The condition has been present for about one day. Symptoms reported: pain and bothersome appearance. The affected area is the back of the torso, head or neck and front of the torso. An image taken at a distance: 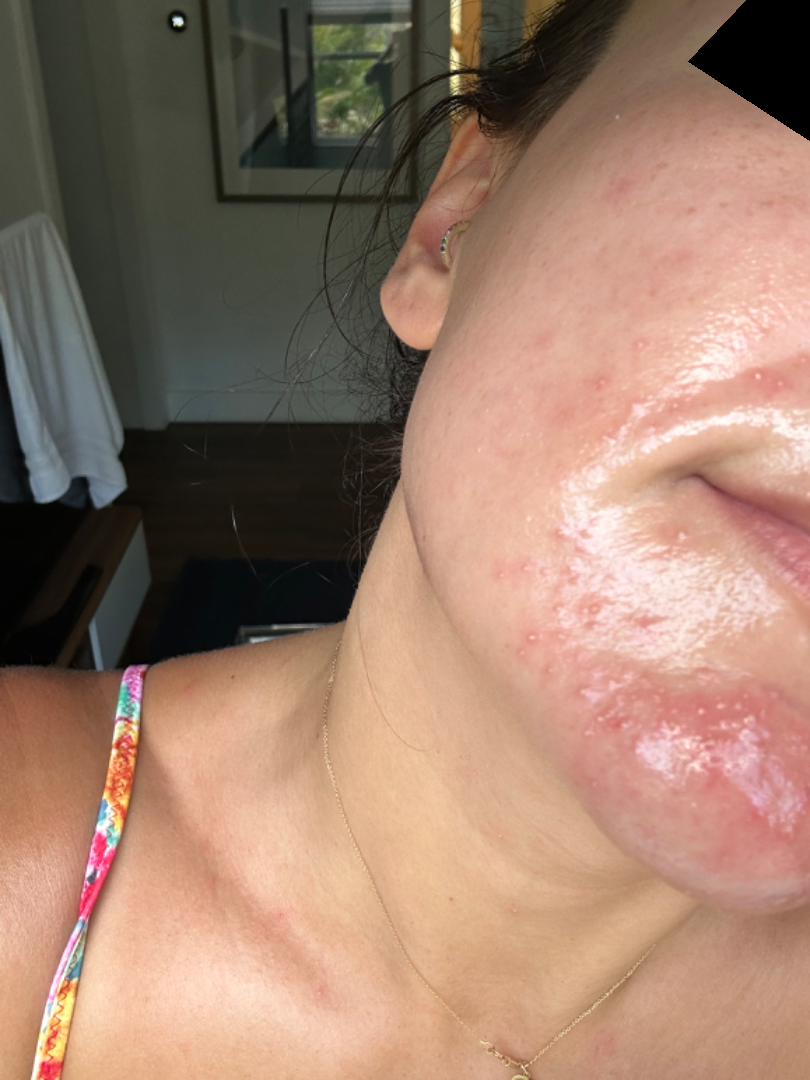{"differential": {"tied_lead": ["Rosacea", "Perioral Dermatitis"]}}